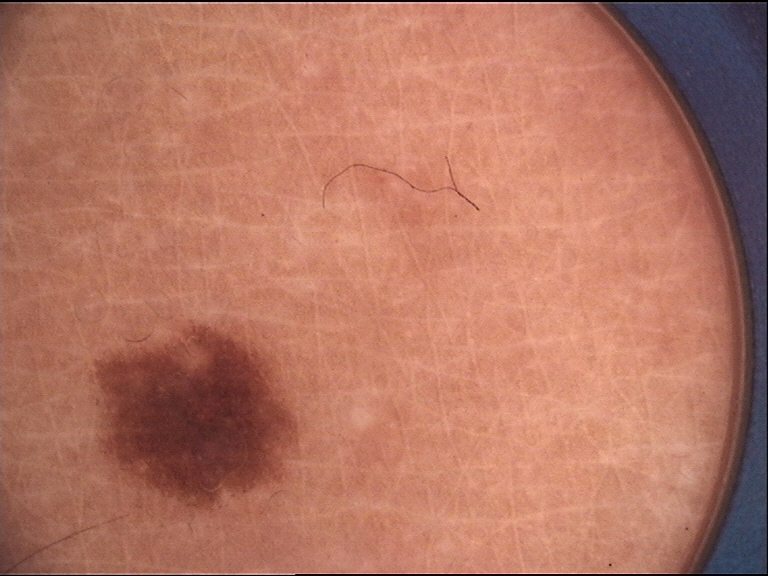{"diagnosis": {"name": "junctional nevus", "code": "jb", "malignancy": "benign", "super_class": "melanocytic", "confirmation": "expert consensus"}}